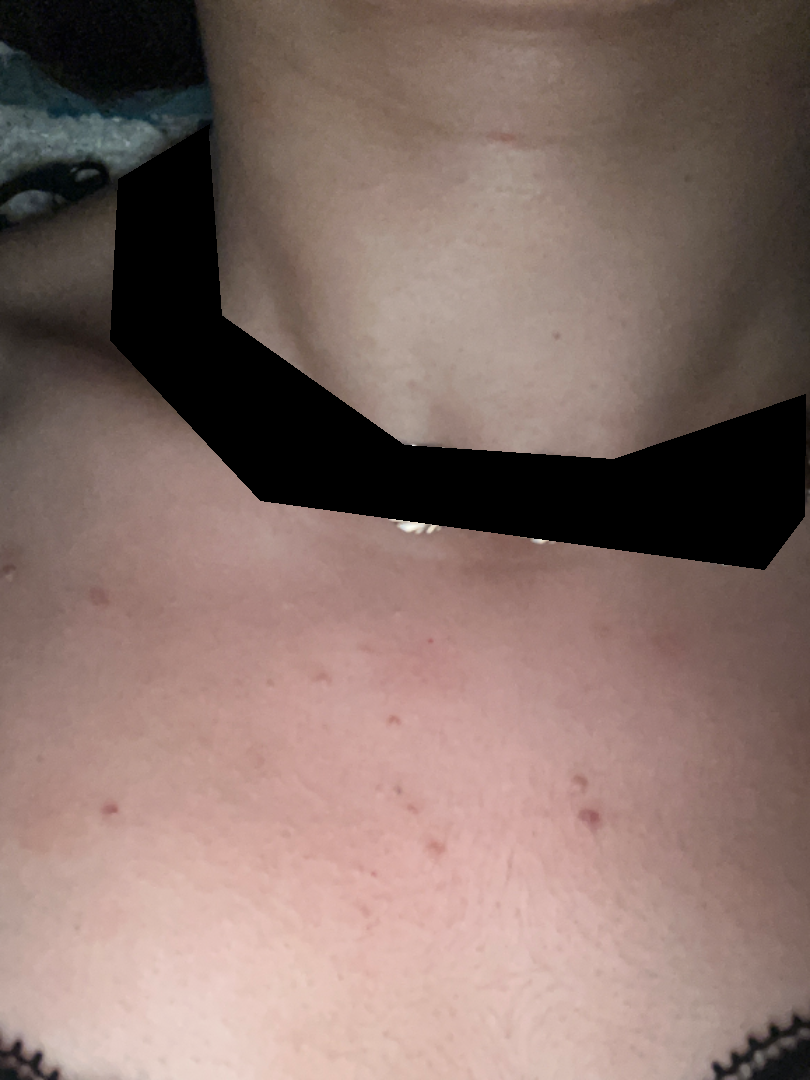Q: What was the assessment?
A: no clear pathology